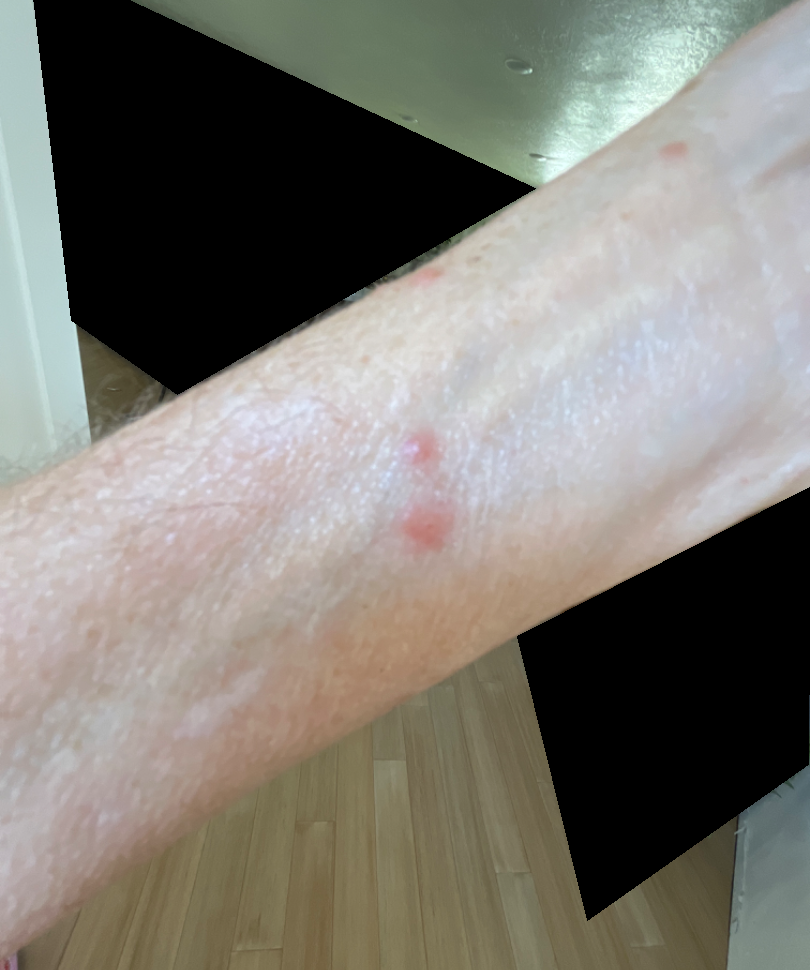The condition has been present for less than one week. The contributor reports itching. A close-up photograph. The patient described the issue as a rash. The patient is a female aged 60–69. The lesion involves the arm. The lesion is described as raised or bumpy. Most likely Insect Bite; less likely is Allergic Contact Dermatitis.